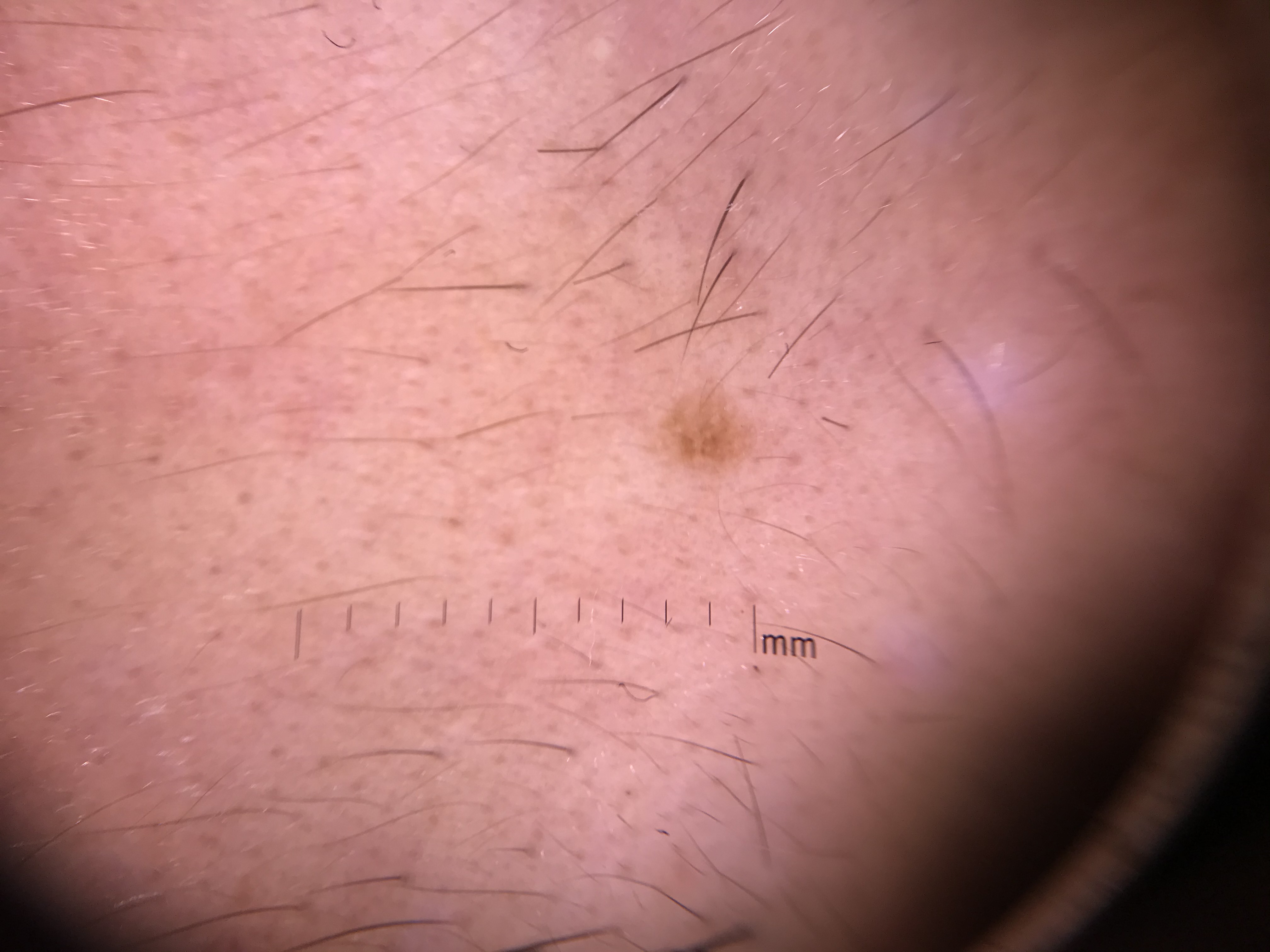{"diagnosis": {"name": "Miescher nevus", "code": "mcb", "malignancy": "benign", "super_class": "melanocytic", "confirmation": "expert consensus"}}